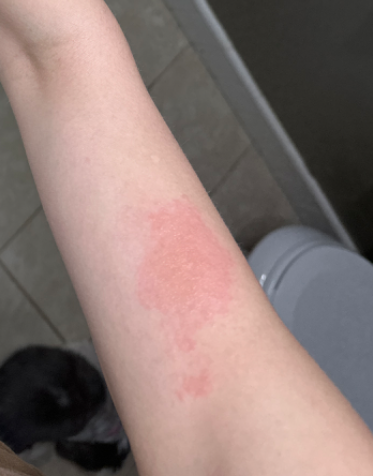<case>
<shot_type>at a distance</shot_type>
<systemic_symptoms>none reported</systemic_symptoms>
<symptoms>itching</symptoms>
<patient_category>a rash</patient_category>
<body_site>arm</body_site>
<texture>raised or bumpy</texture>
<differential>
  <leading>Allergic Contact Dermatitis</leading>
  <considered>Acute dermatitis, NOS</considered>
</differential>
</case>